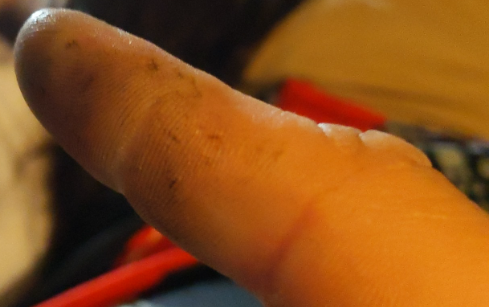The skin findings could not be characterized from the image.
The condition has been present for less than one week.
The photo was captured at an angle.
Reported lesion symptoms include enlargement, burning, darkening, pain and bothersome appearance.